A dermoscopic image of a skin lesion. The patient describes having numerous moles. A female patient 78 years of age. Acquired for a research image collection, with no referral diagnosis.
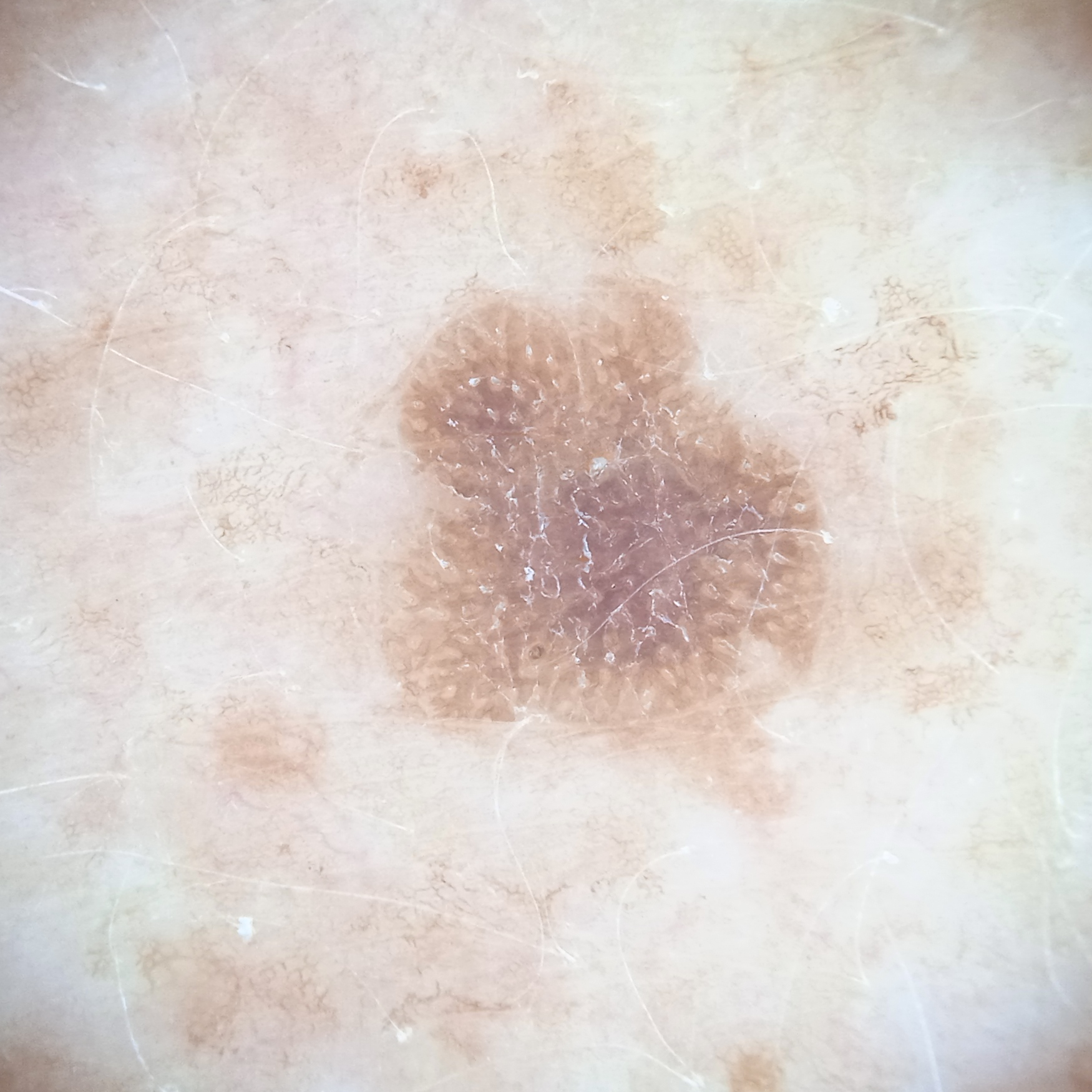The lesion is on the back. The dermatologists' assessment was a seborrheic keratosis.